A dermoscopy image of a single skin lesion.
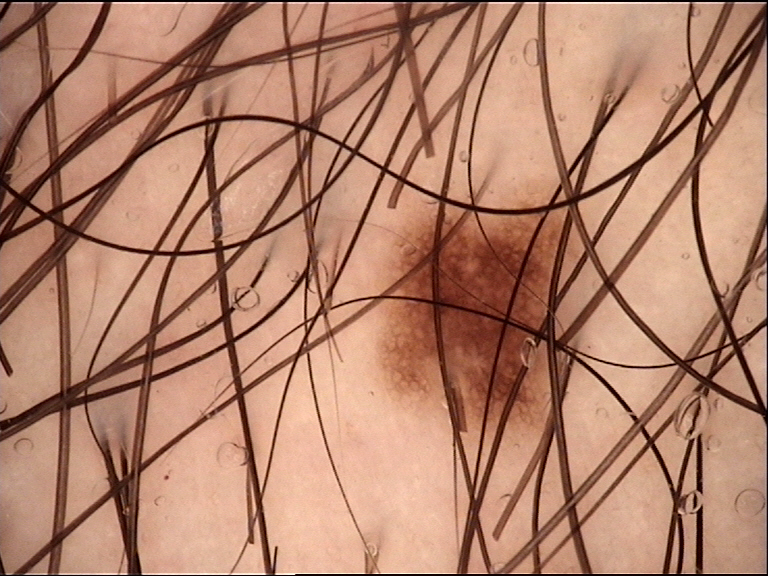Conclusion:
The diagnosis was a benign lesion — a dysplastic junctional nevus.